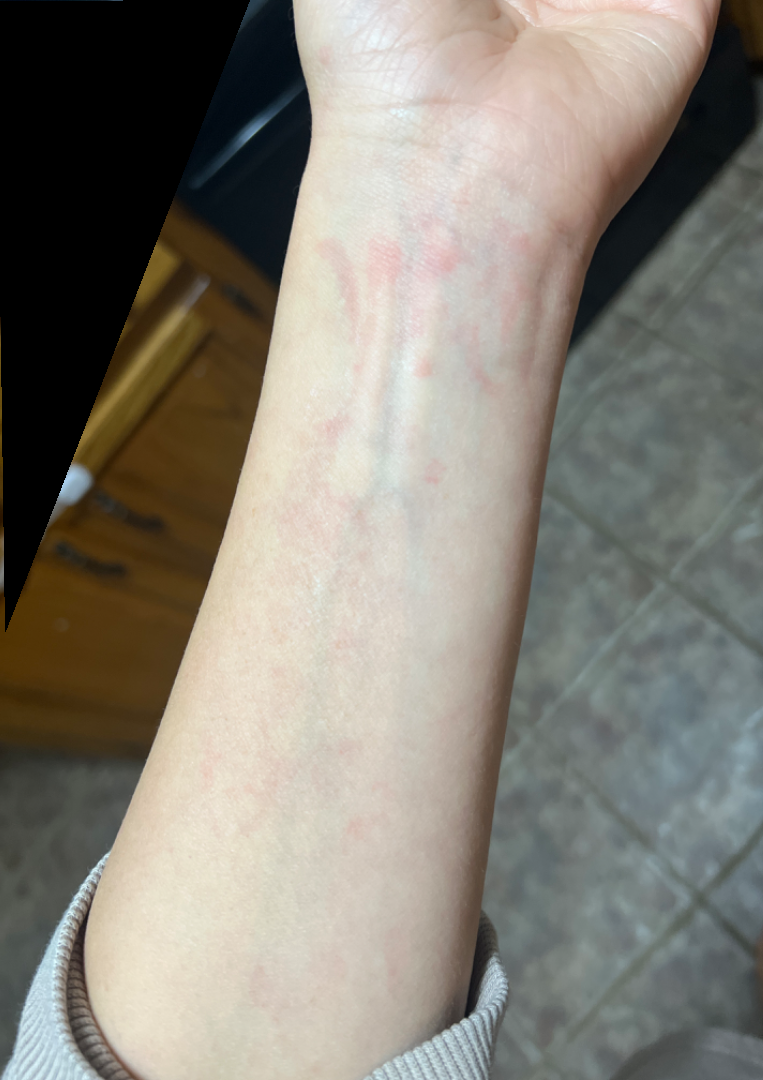The patient notes the lesion is flat. The lesion involves the head or neck and arm. Close-up view. On photographic review by a dermatologist, Insect Bite (33%); Irritant Contact Dermatitis (33%); Allergic Contact Dermatitis (33%).